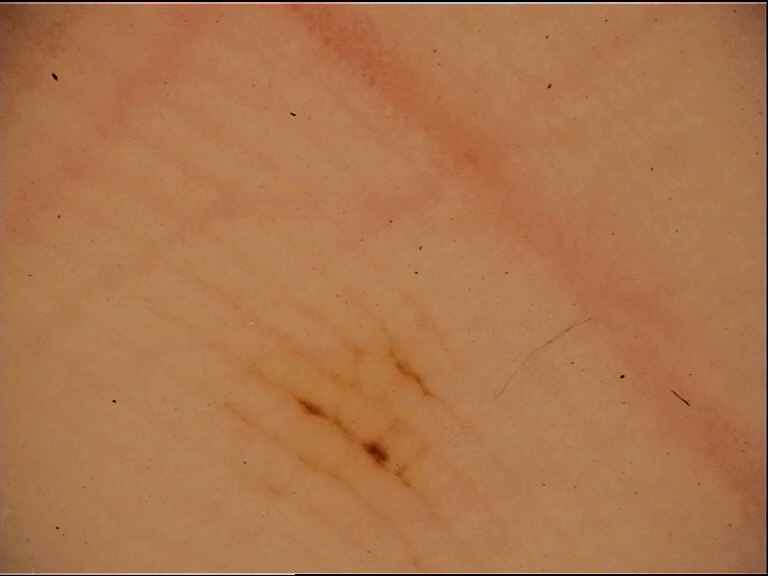Q: What is this lesion?
A: acral junctional nevus (expert consensus)